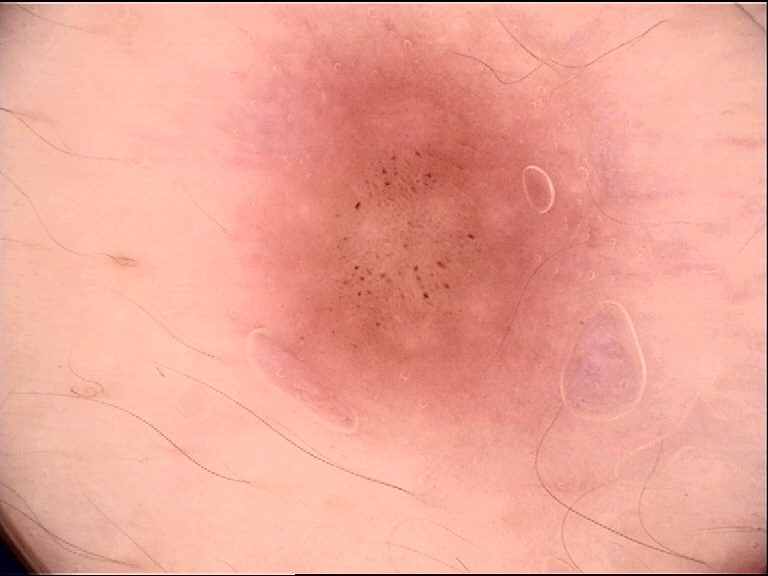<case>
  <image>dermatoscopy</image>
  <lesion_type>
    <main_class>banal</main_class>
    <pattern>compound</pattern>
  </lesion_type>
  <diagnosis>
    <name>compound nevus</name>
    <code>cb</code>
    <malignancy>benign</malignancy>
    <super_class>melanocytic</super_class>
    <confirmation>expert consensus</confirmation>
  </diagnosis>
</case>